Dermoscopy of a skin lesion:
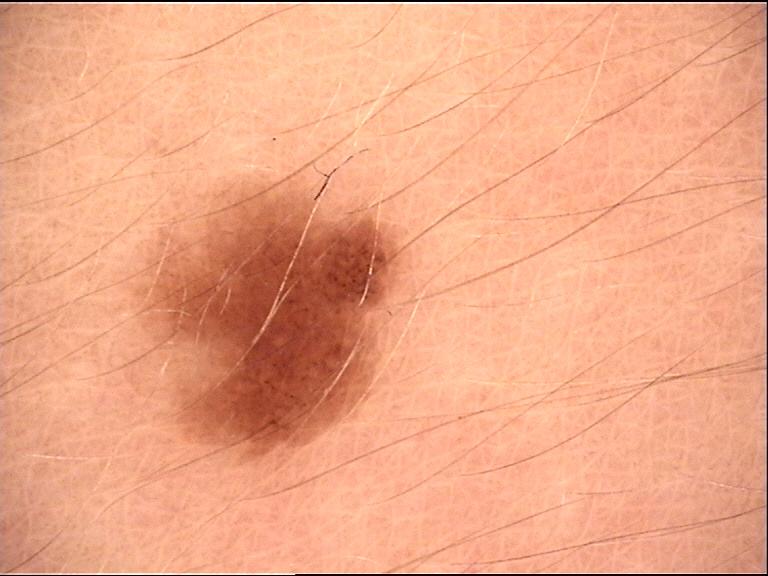Labeled as a dysplastic junctional nevus.